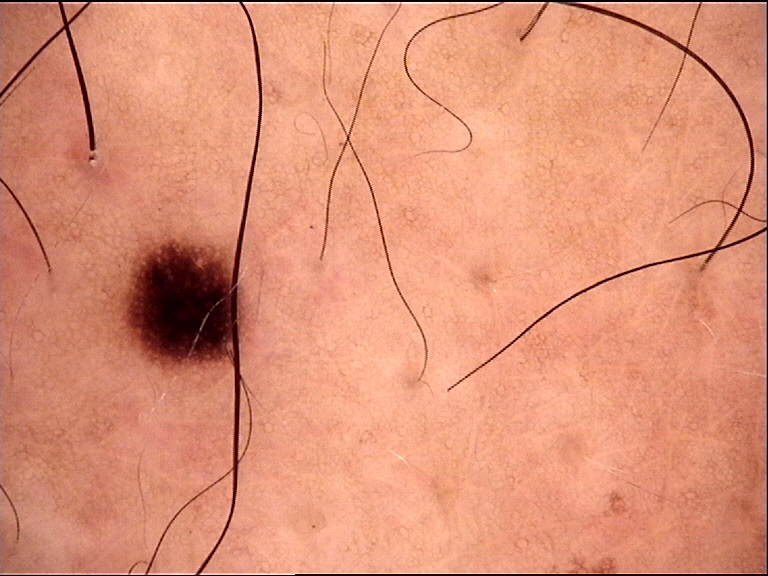Summary: A dermoscopic image of a skin lesion. Conclusion: Labeled as a banal lesion — a junctional nevus.